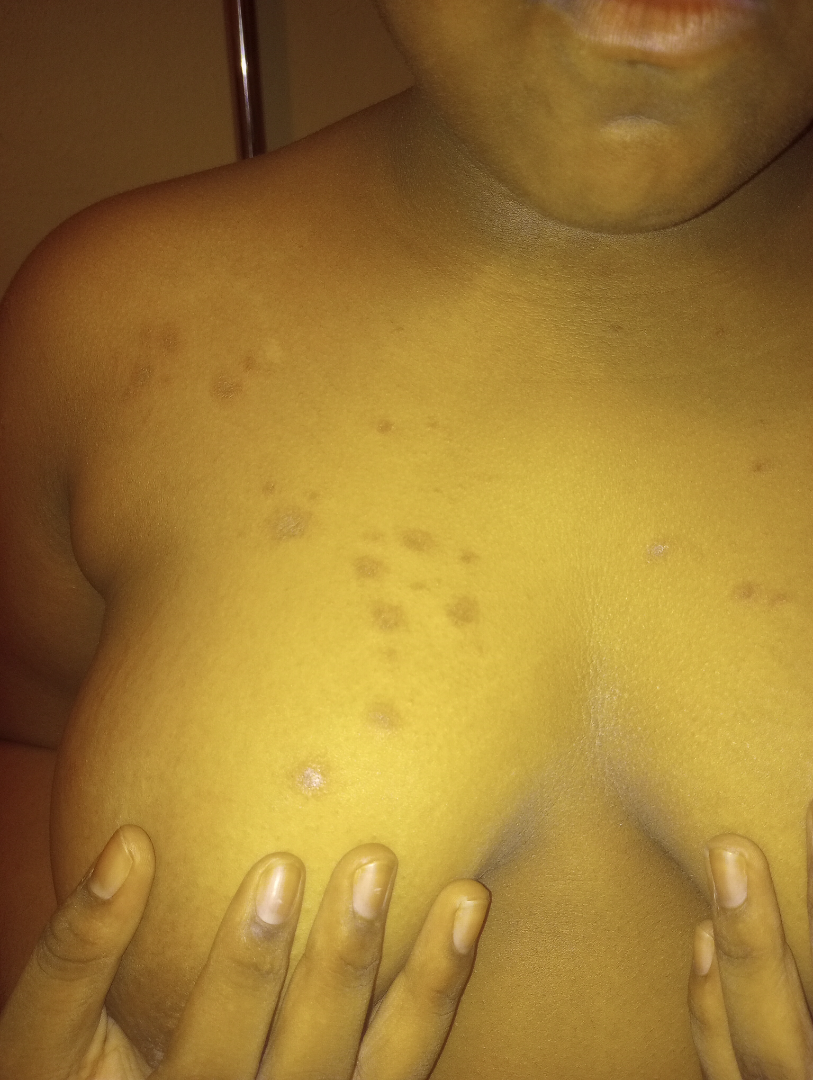– image framing: close-up
– differential diagnosis: Psoriasis, Drug Rash and Syphilis were considered with similar weight